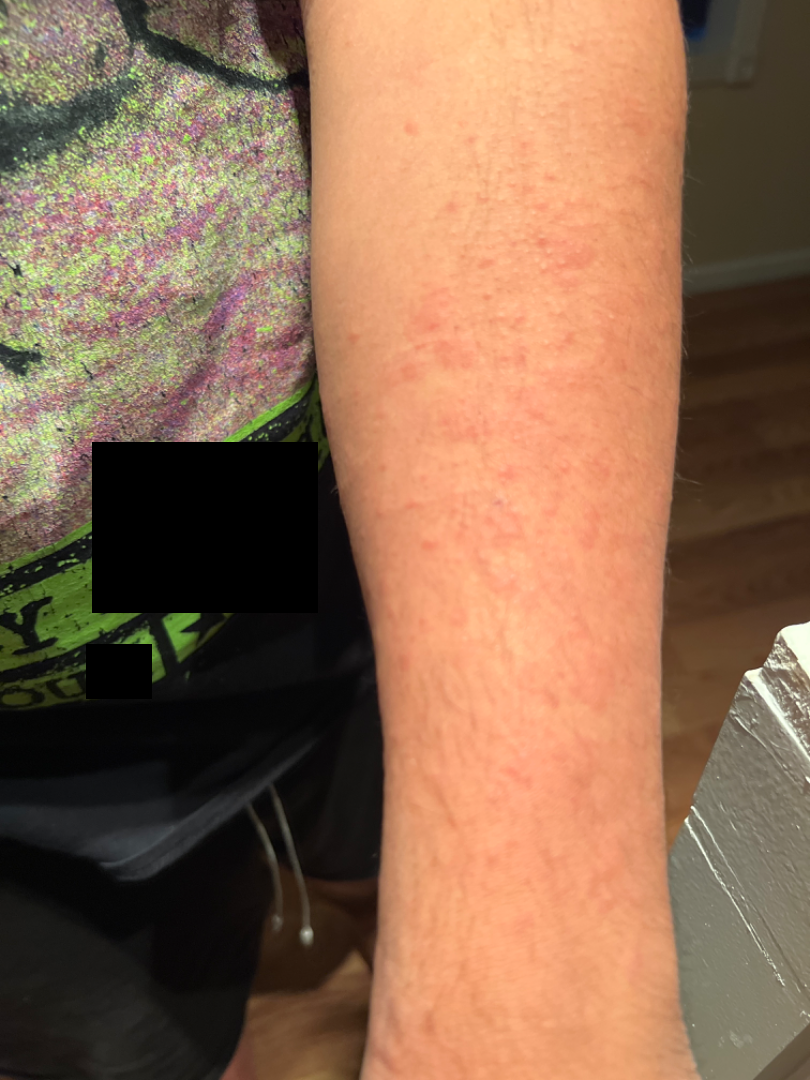Case summary:
- photo taken · close-up
- assessment · Urticaria (possible); Allergic Contact Dermatitis (possible); Drug Rash (remote)